Self-categorized by the patient as a rash · this is a close-up image · the contributor reports itching, bothersome appearance and darkening · the subject is a female aged 18–29 · no constitutional symptoms were reported · texture is reported as flat · the condition has been present for one to four weeks:
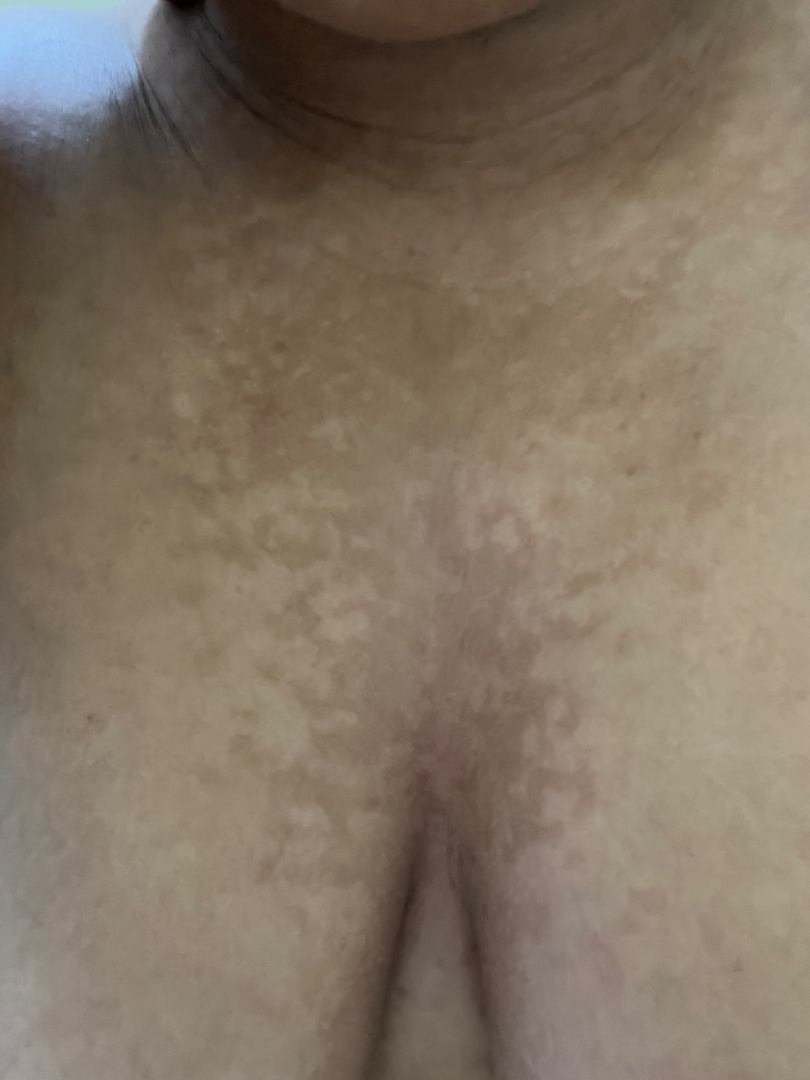Assessment: On photographic review by a dermatologist, Confluent and reticulate papillomatosis (primary).